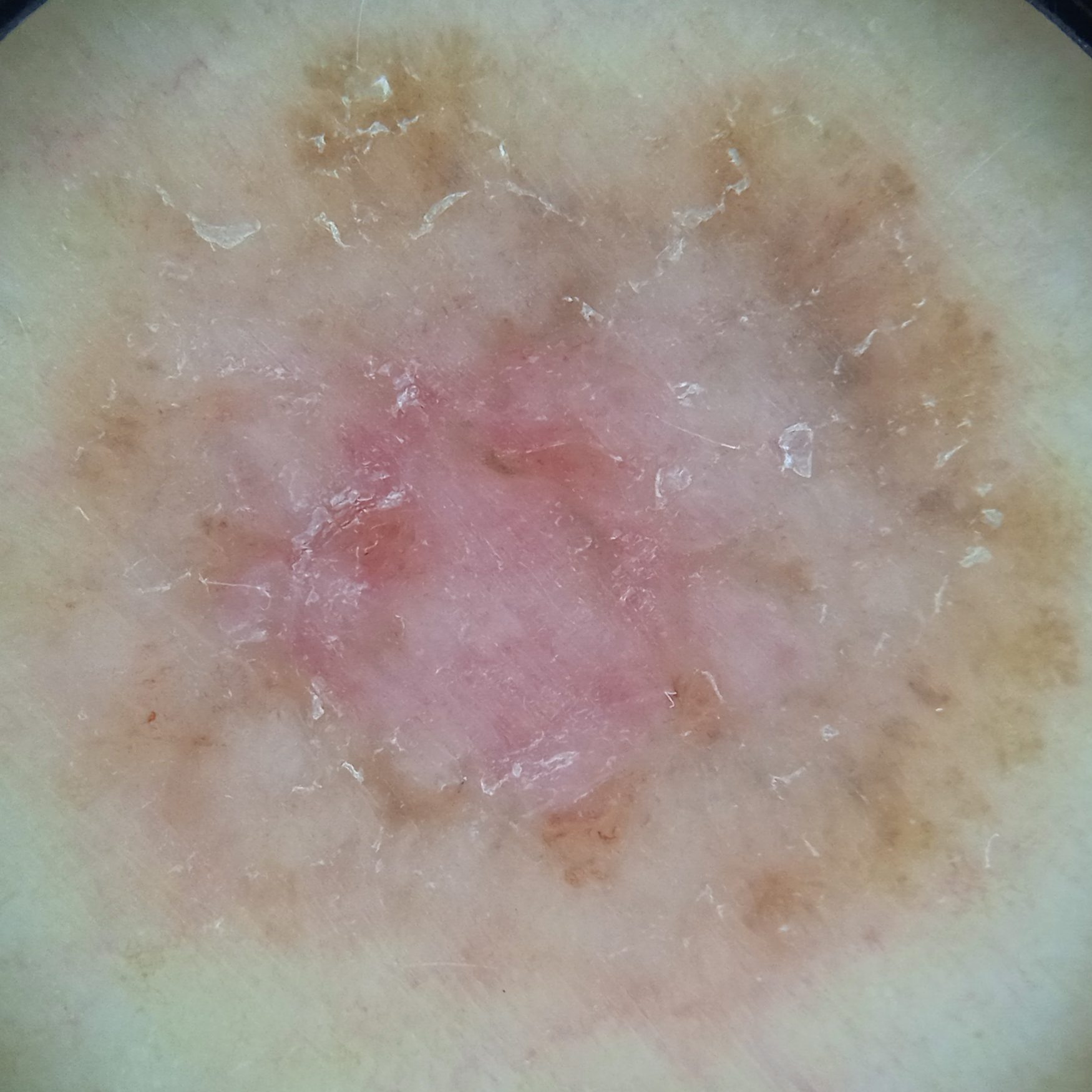The diagnostic impression was a basal cell carcinoma.